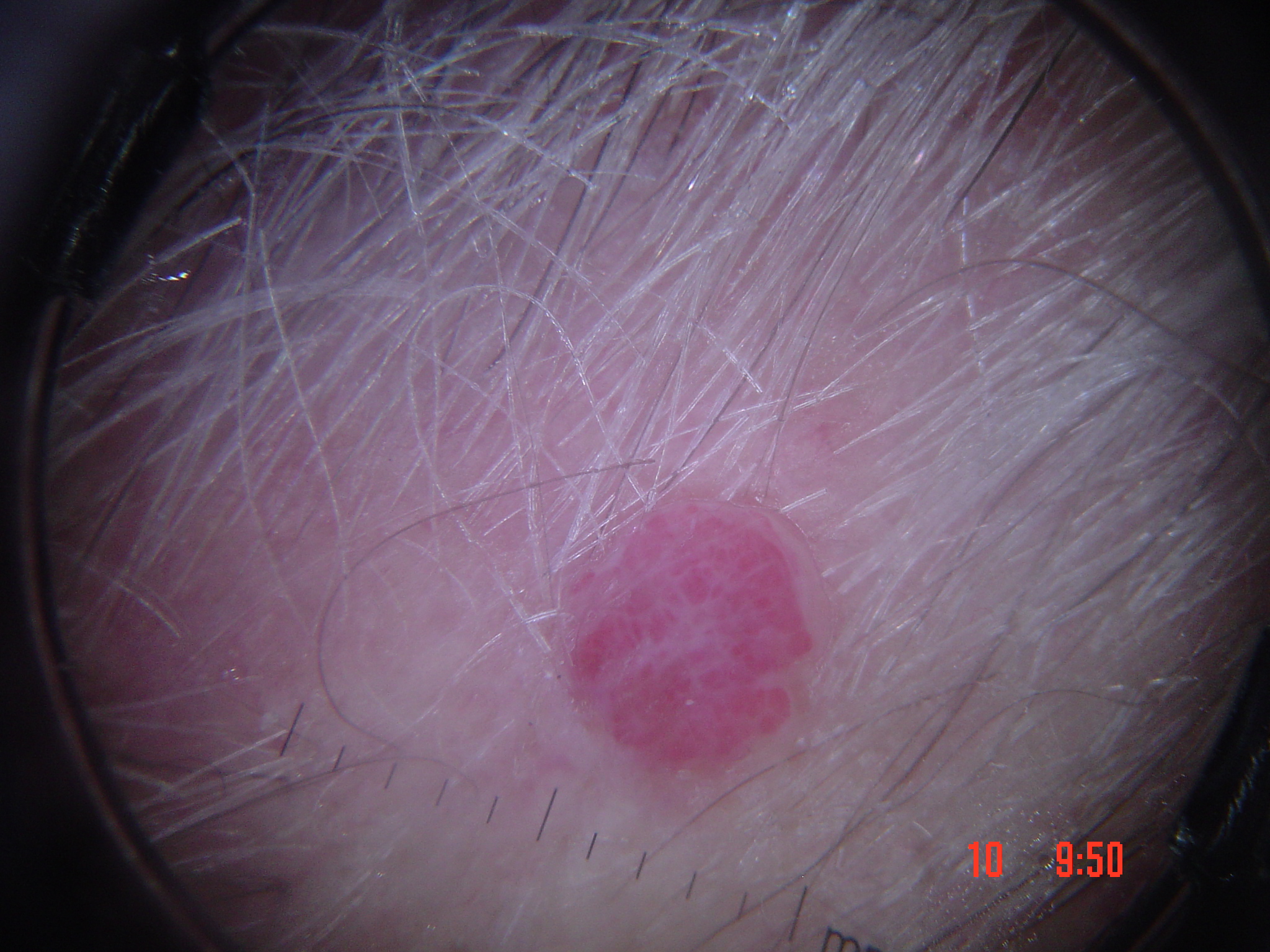The diagnosis was a hemangioma.